The subject is female. The photo was captured at a distance. The arm, back of the hand, leg and head or neck are involved:
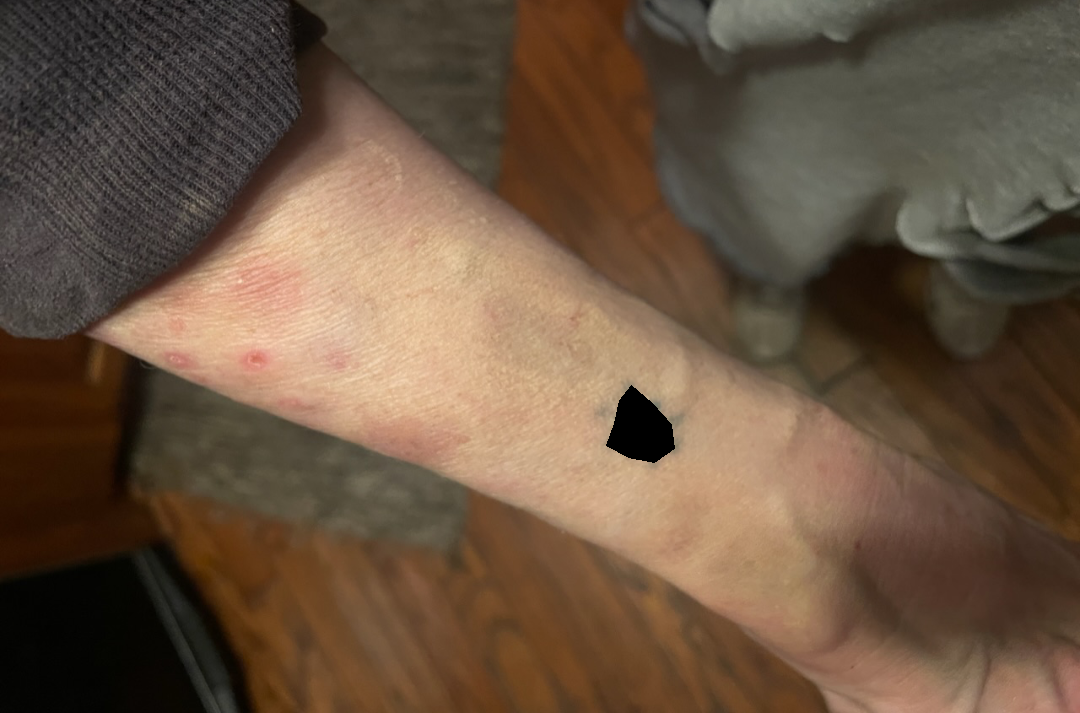No differential diagnosis could be assigned on photographic review.